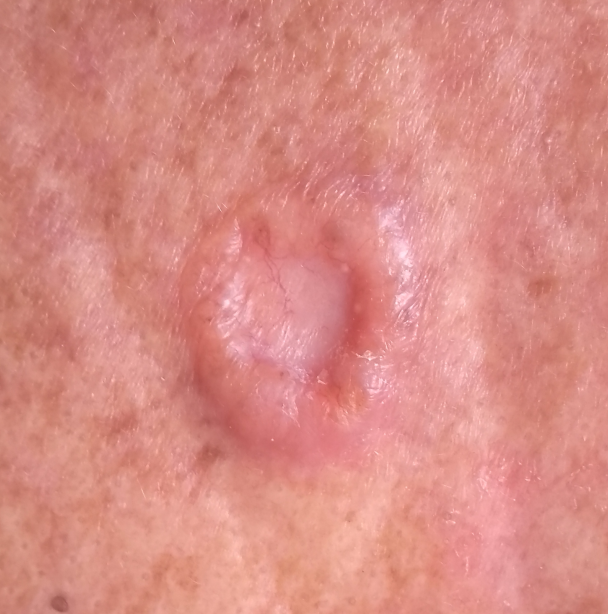A male patient 74 years of age.
Skin type II.
The lesion is roughly 19 by 17 mm.
Histopathologically confirmed as a malignant skin lesion — a basal cell carcinoma.